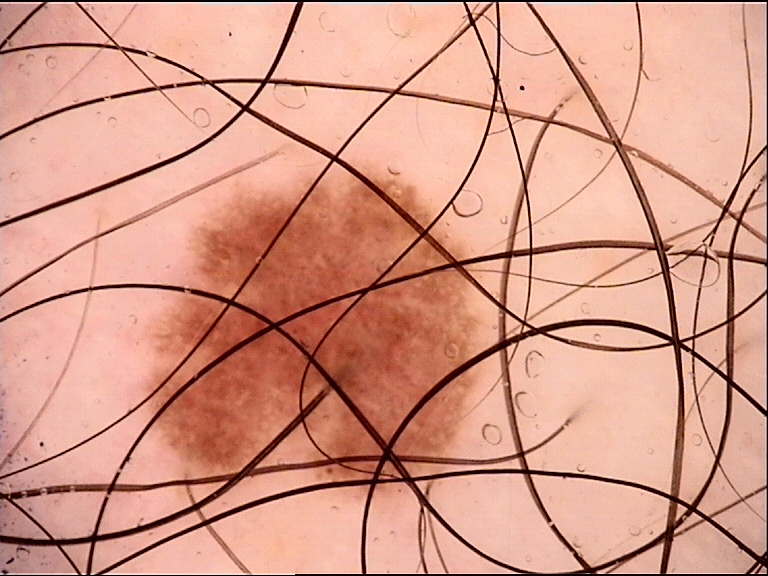| key | value |
|---|---|
| image type | dermoscopy |
| diagnostic label | dysplastic junctional nevus (expert consensus) |